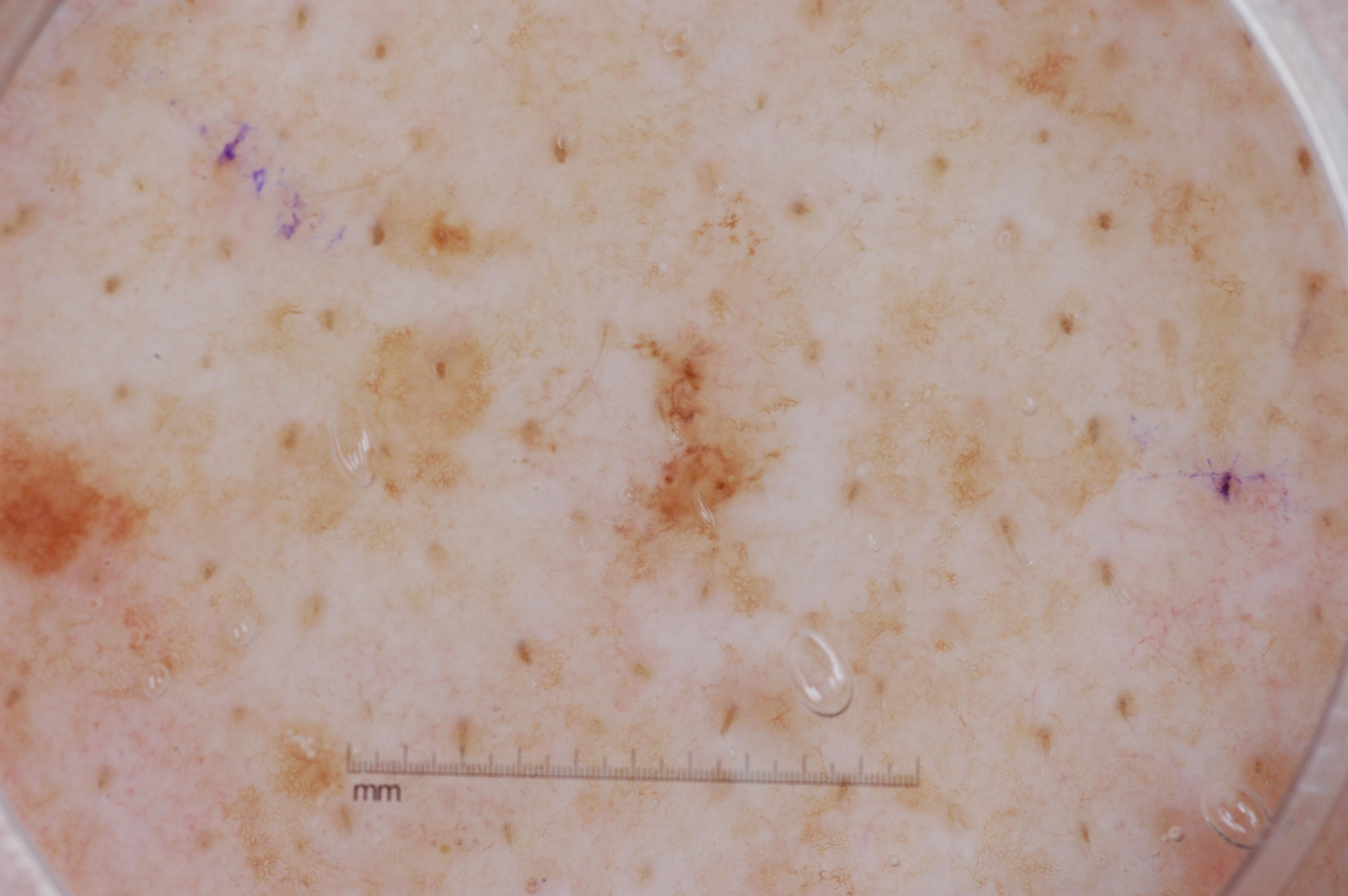{"image": {"modality": "dermoscopy"}, "patient": {"sex": "male", "age_approx": 70}, "lesion_location": {"bbox_xyxy": [509, 166, 857, 633]}, "dermoscopic_features": {"present": ["pigment network"], "absent": ["negative network", "streaks", "milia-like cysts"]}, "diagnosis": {"name": "melanoma", "malignancy": "malignant", "lineage": "melanocytic", "provenance": "histopathology"}}